Female contributor, age 50–59; the arm is involved; this image was taken at an angle.
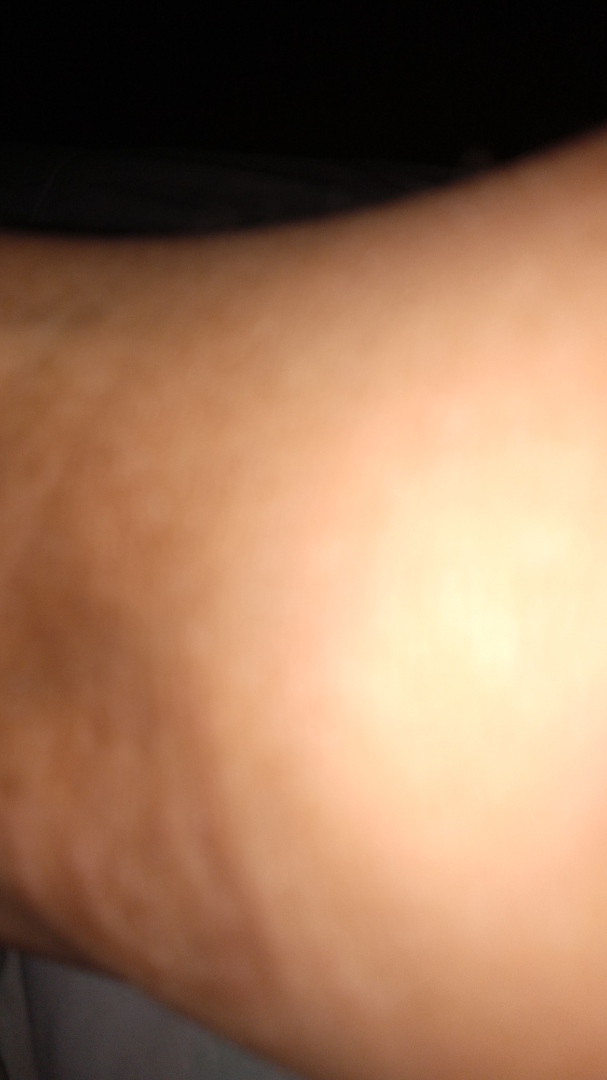Assessment: The case was indeterminate on photographic review.